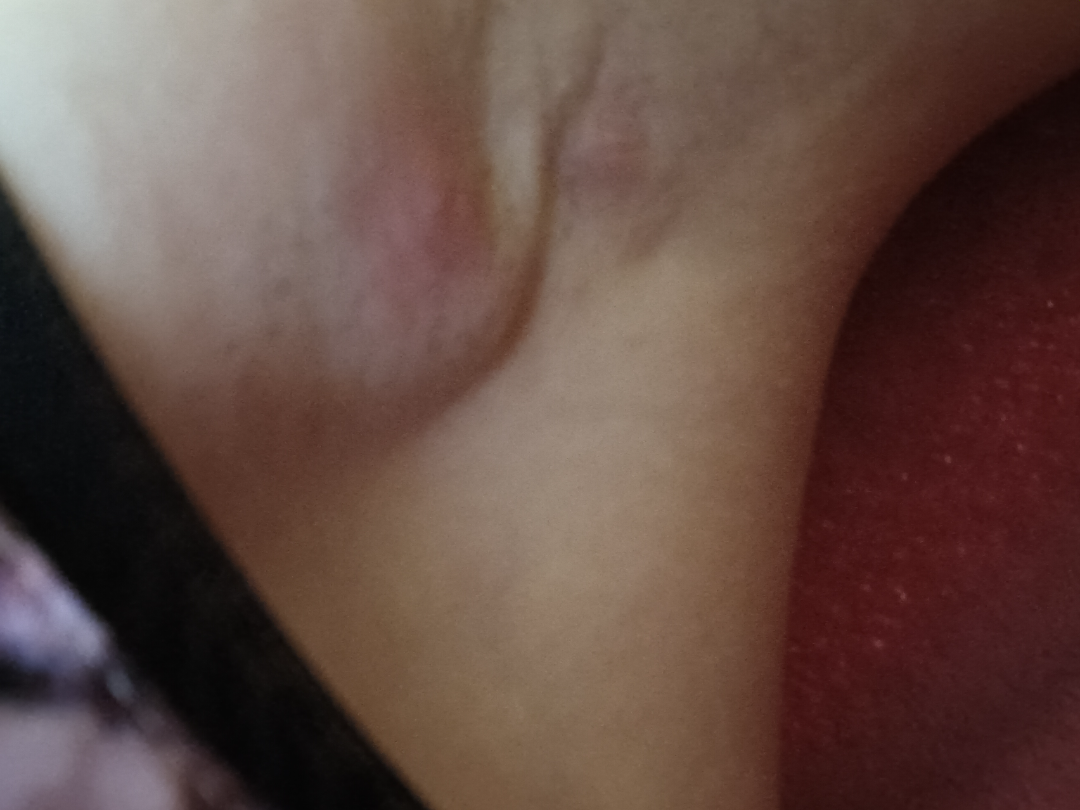The lesion involves the arm.
The condition has been present for less than one week.
The contributor notes the lesion is raised or bumpy.
This is a close-up image.
The contributor notes pain and enlargement.
The subject is female.
The leading impression is Hidradenitis; possibly Abscess; also consider Cutaneous T Cell Lymphoma.